Male contributor, age 18–29 · close-up view · the affected area is the leg: 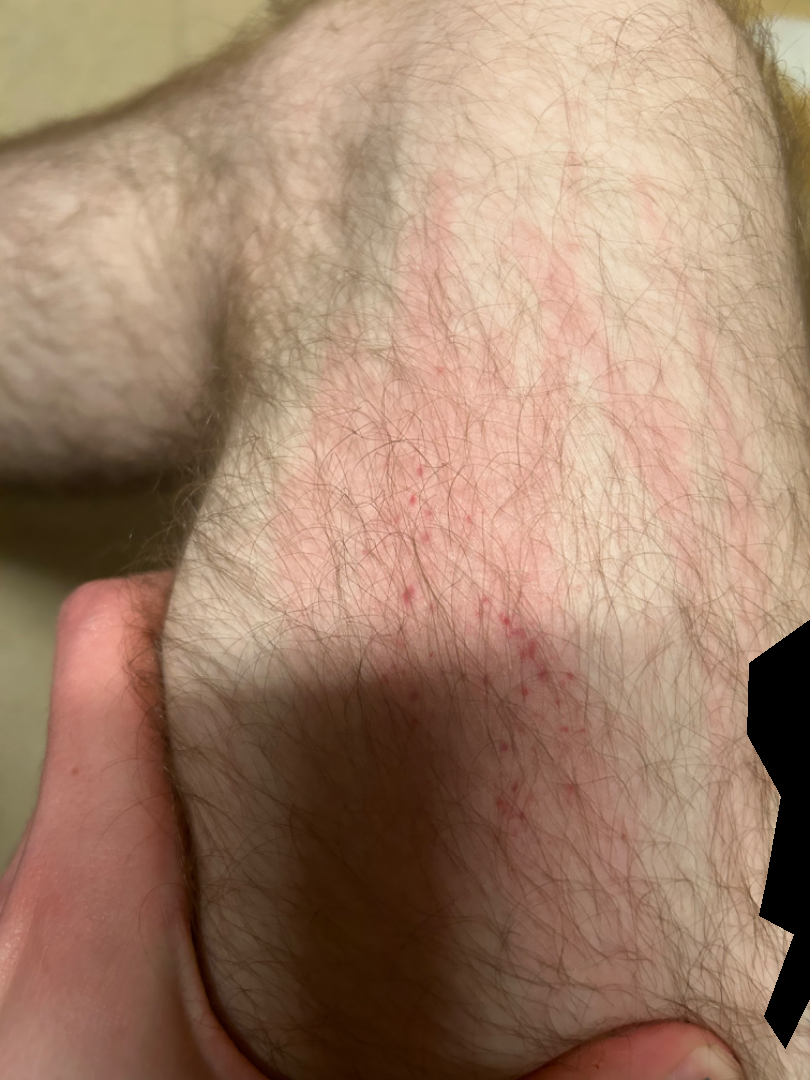Review: The skin findings could not be characterized from the image.